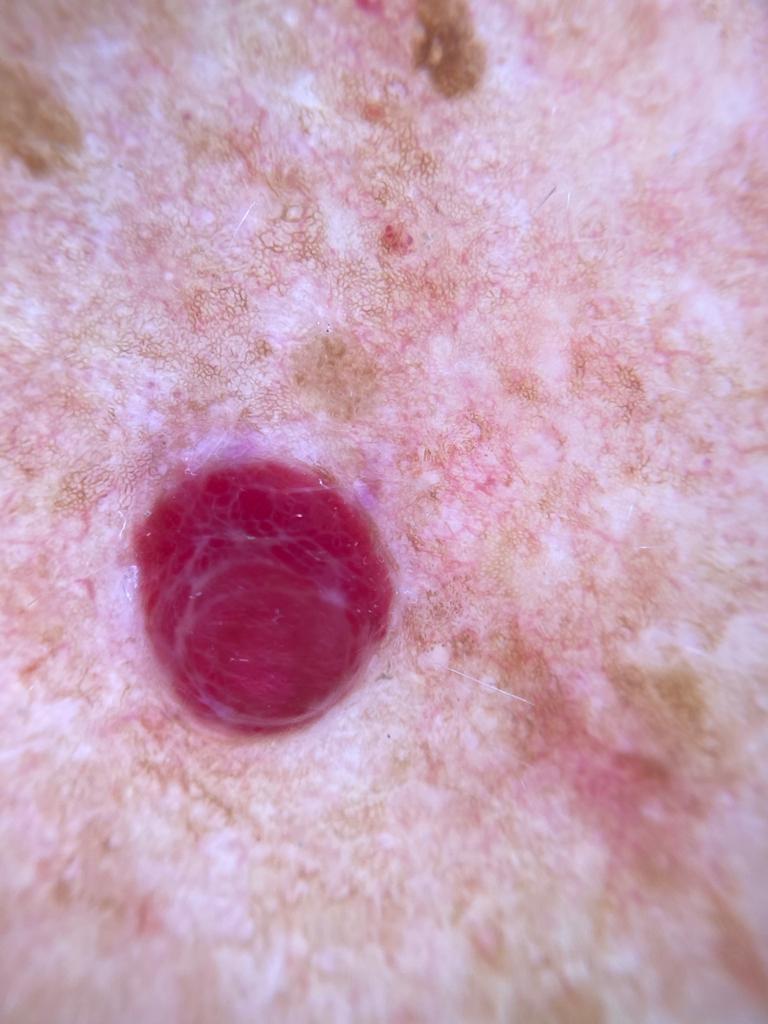Fitzpatrick = II
patient = male, aged approximately 75
image = dermatoscopic image
assessment = vascular lesion